Close-up view · the lesion is associated with bothersome appearance · the subject is 30–39, female · the condition has been present for less than one week: 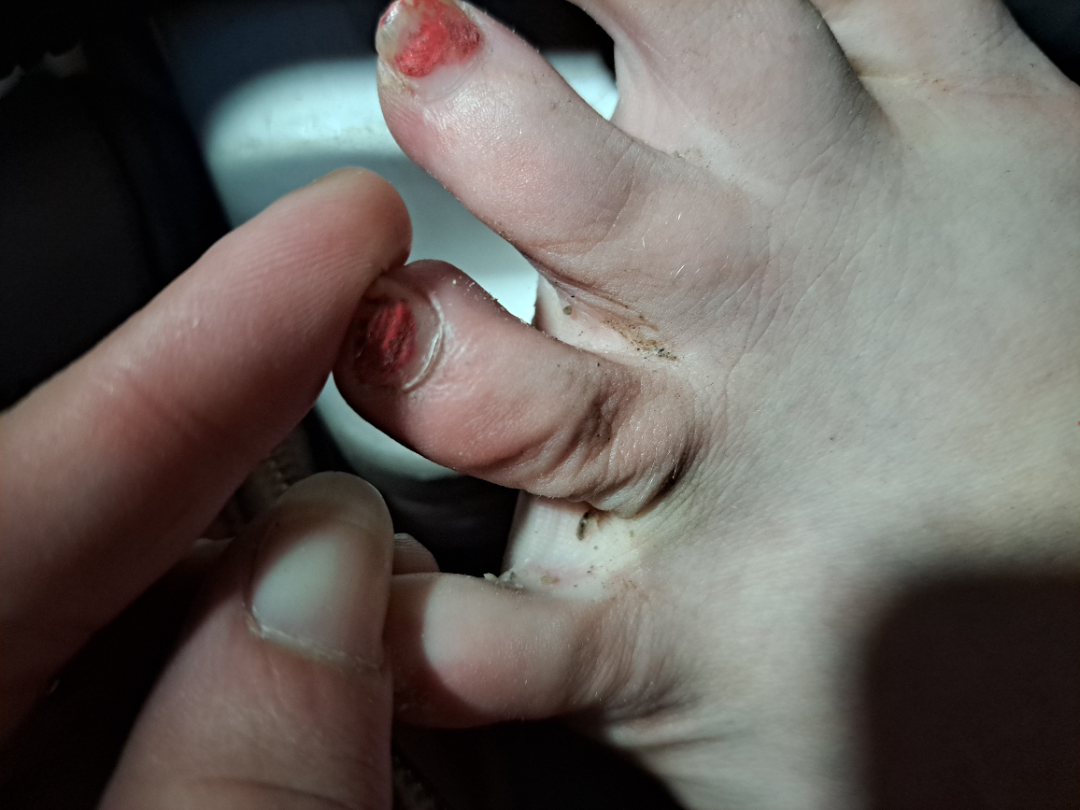The case was indeterminate on photographic review.